A male patient aged around 50. Dermoscopy of a skin lesion.
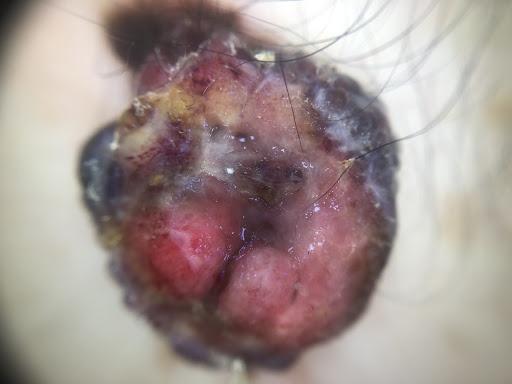Q: Where on the body is the lesion?
A: the lateral trunk
Q: What is the diagnosis?
A: Melanoma (biopsy-proven)